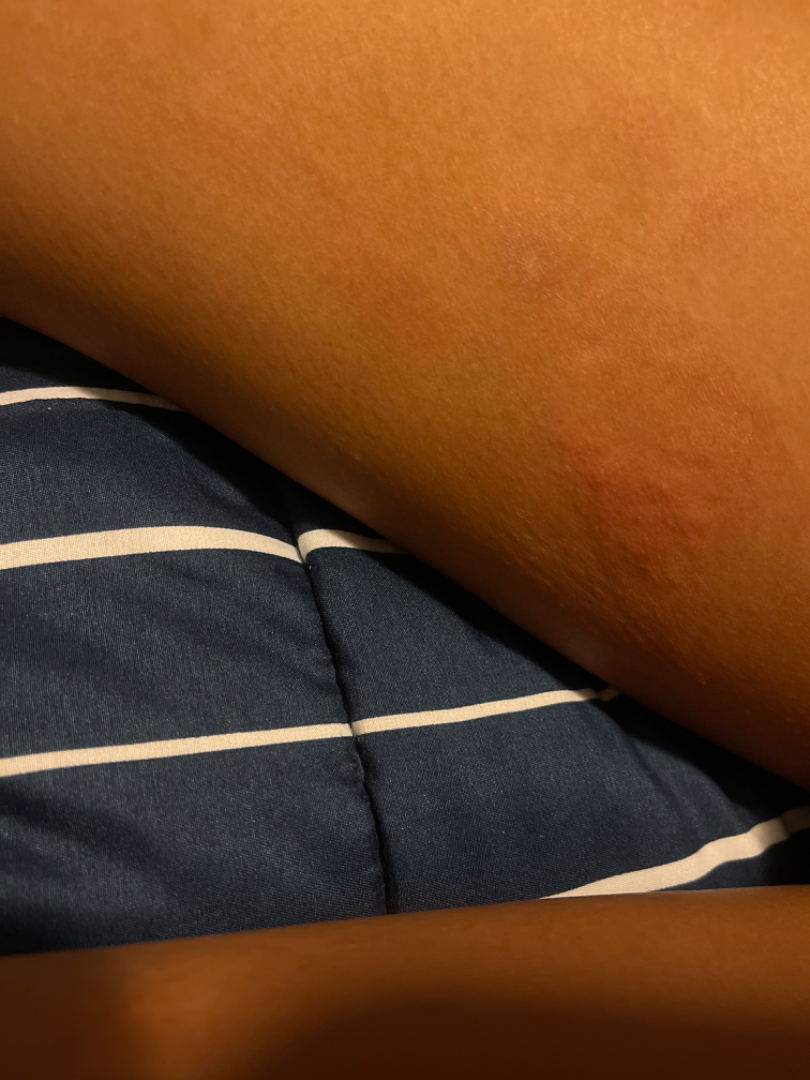The condition has been present for one to four weeks. The lesion involves the leg. Symptoms reported: darkening and itching. The subject is a female aged 30–39. The photo was captured at a distance. Skin tone: Fitzpatrick phototype III; non-clinician graders estimated 5 on the Monk skin tone scale. Most consistent with Allergic Contact Dermatitis; also consider Eczema; an alternative is Acute dermatitis, NOS; less probable is Urticaria; a more distant consideration is Tinea.